Skin tone: FST III. Close-up view:
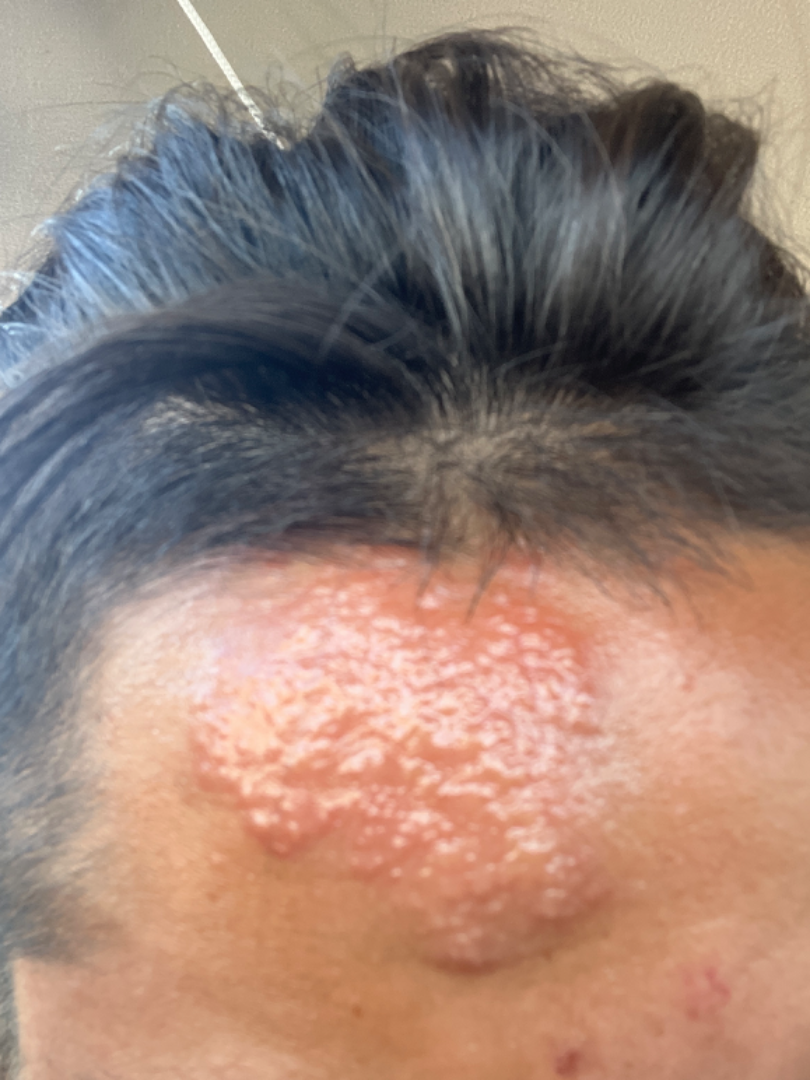On teledermatology review, the impression was split between Skin infection, Cutaneous sarcoidosis and Granulomatous disorder of the skin and subcutaneous tissue.